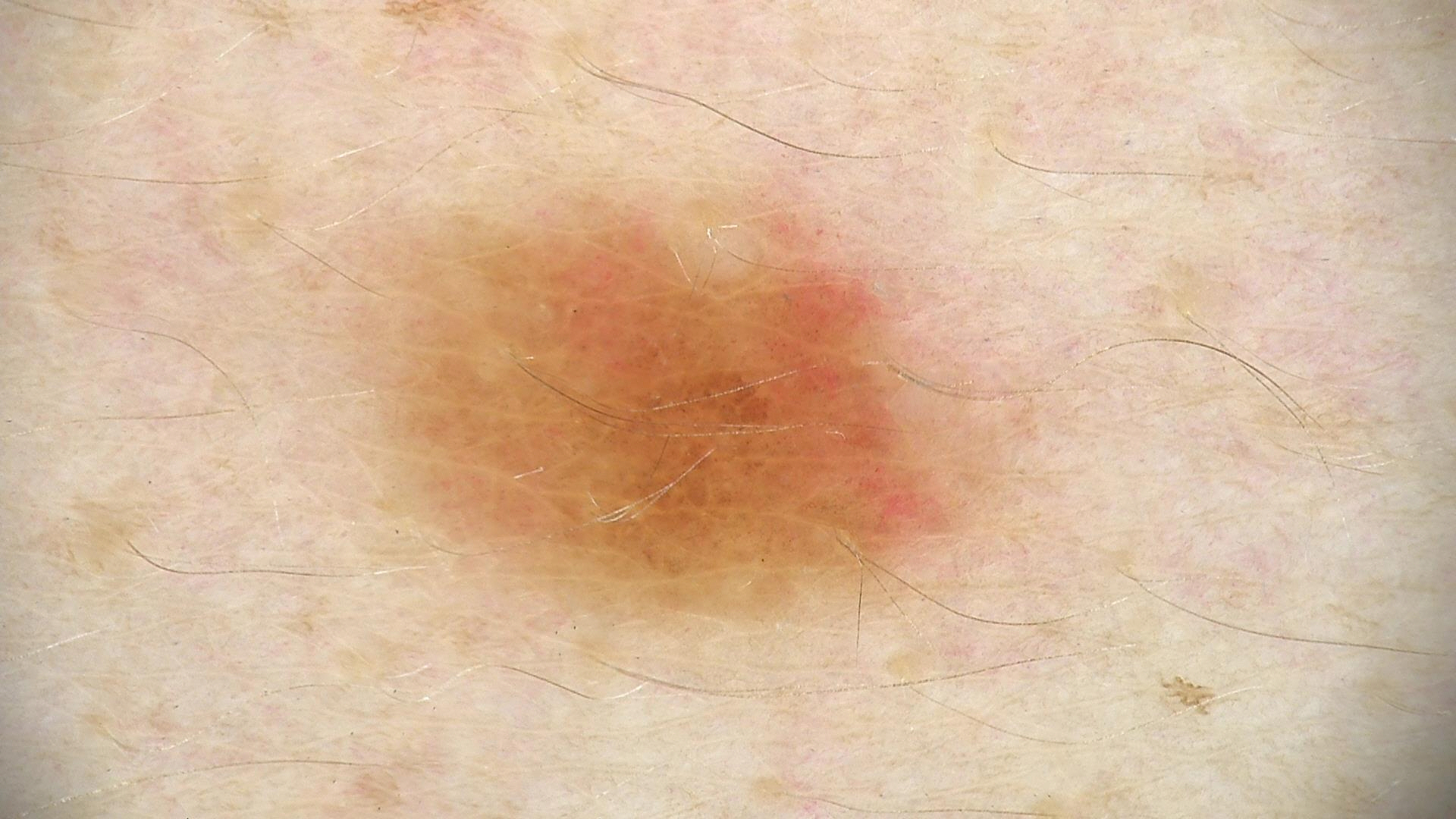image = dermatoscopy; diagnostic label = dysplastic junctional nevus (expert consensus).